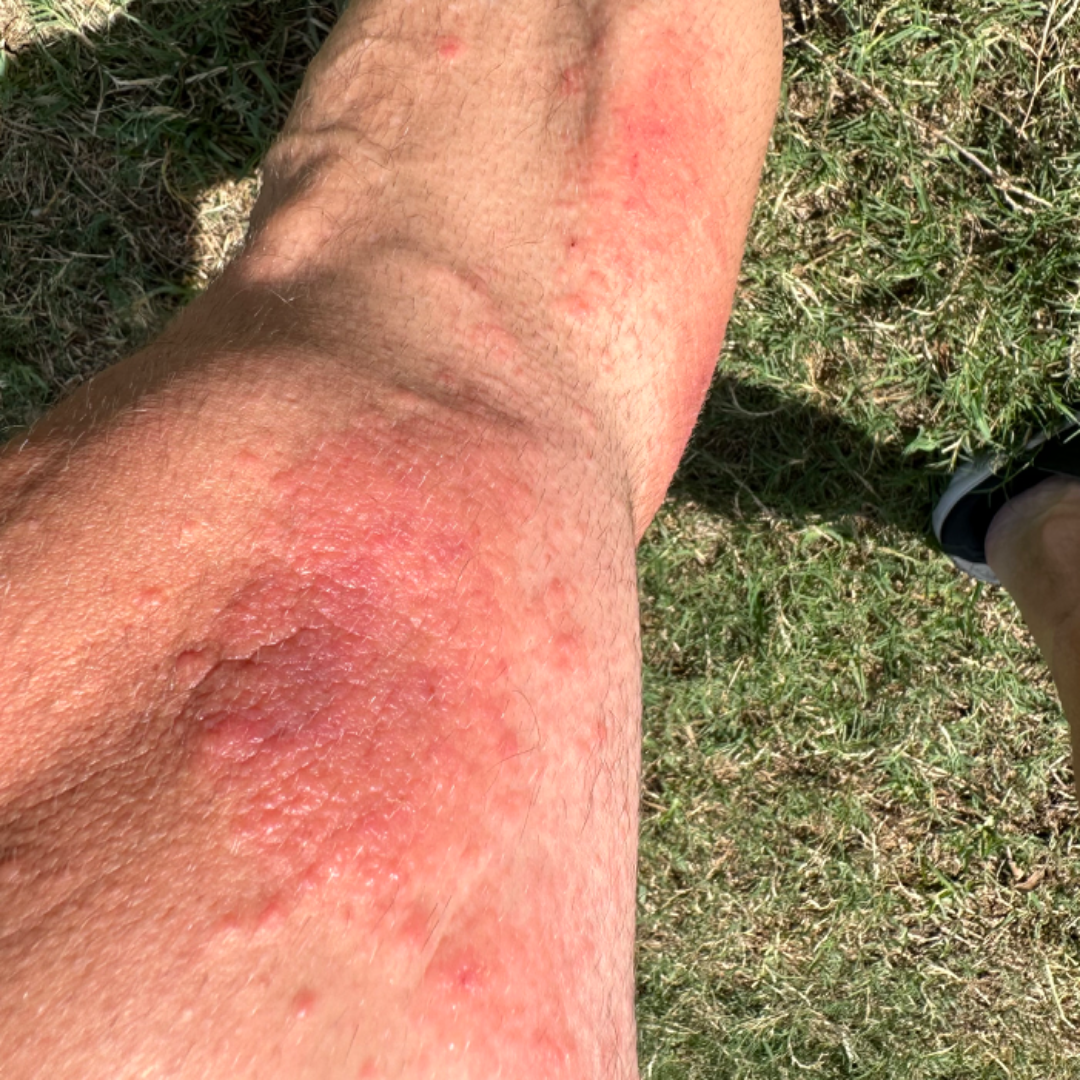The image was not sufficient for the reviewer to characterize the skin condition. The lesion involves the leg and arm. The patient considered this a rash. Skin tone: Fitzpatrick phototype III. The patient reported no systemic symptoms. The lesion is described as raised or bumpy. The photograph was taken at an angle. The lesion is associated with enlargement, itching and bothersome appearance. The subject is a male aged 40–49. The condition has been present for less than one week.